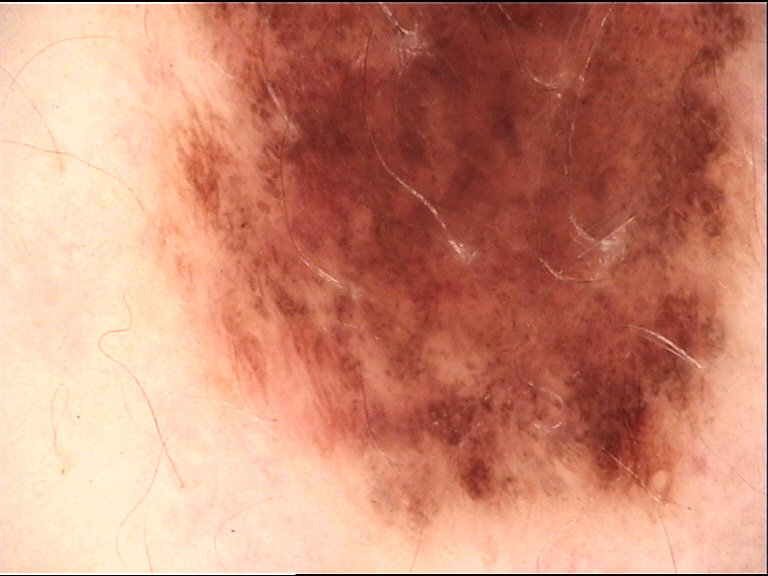Dermoscopy of a skin lesion.
Diagnosed as a benign lesion — a dysplastic junctional nevus.